A skin lesion imaged with a dermatoscope.
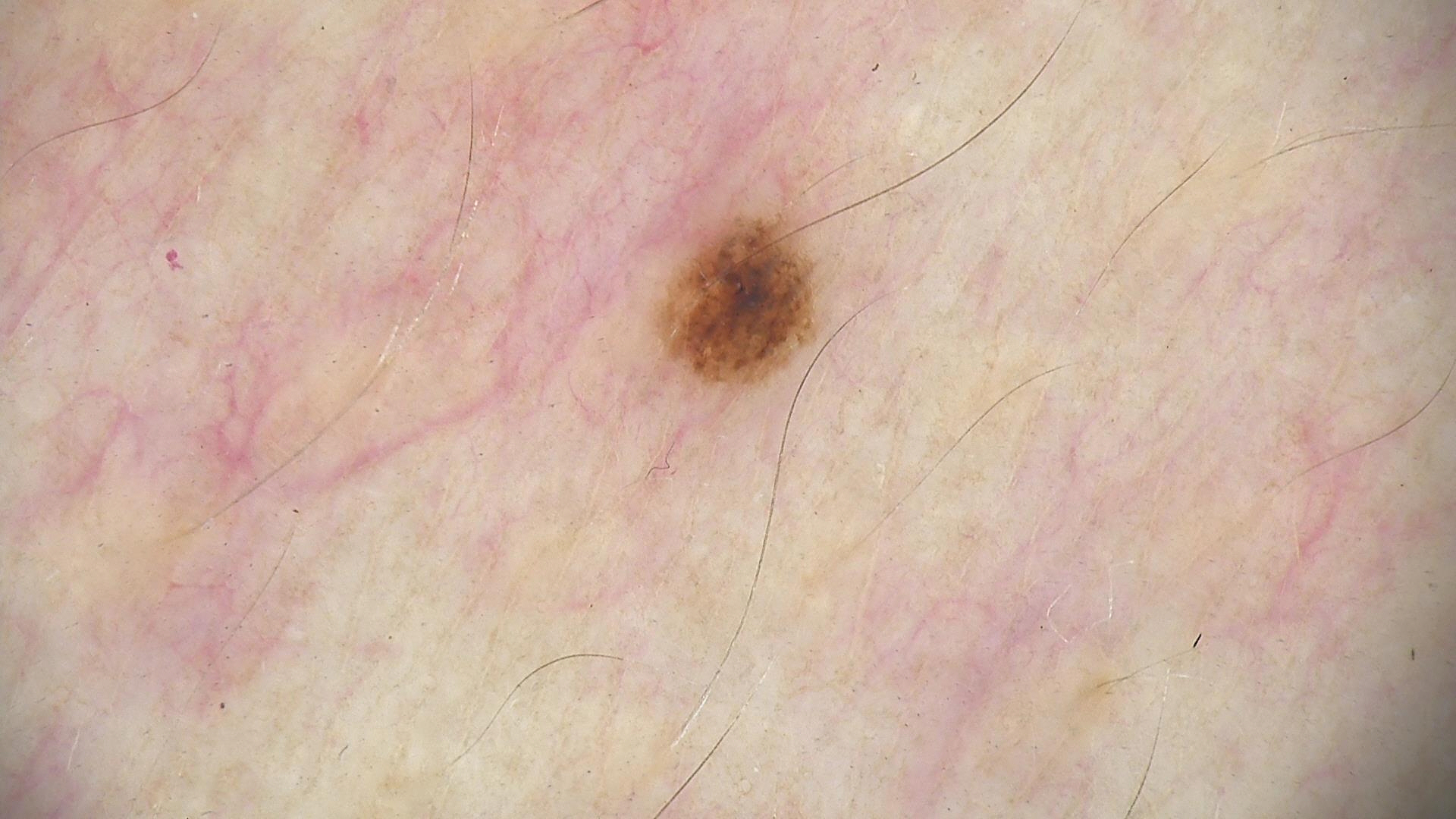Conclusion:
Classified as a dysplastic junctional nevus.